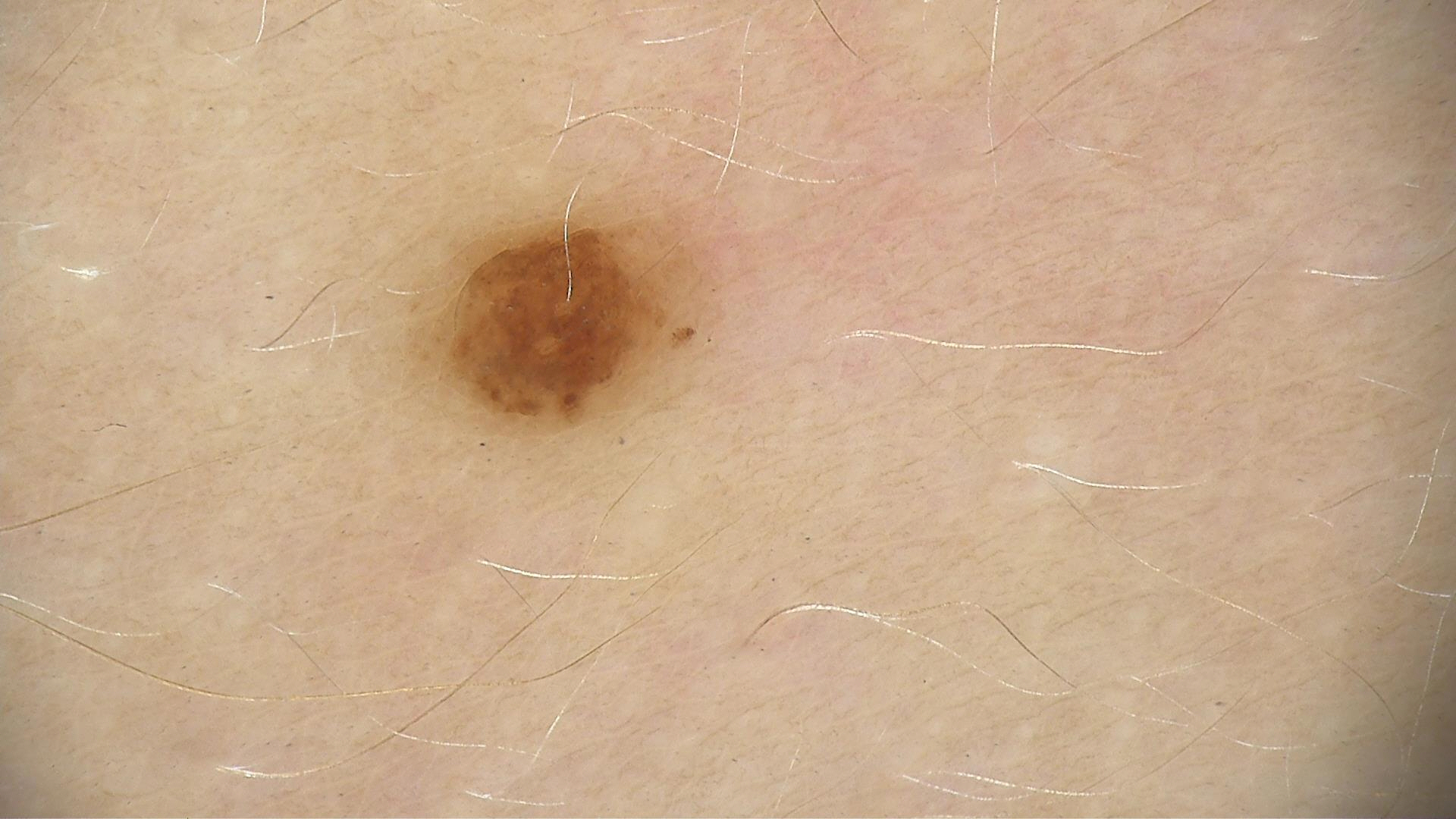A dermoscopy image of a single skin lesion.
Diagnosed as a benign lesion — a dysplastic junctional nevus.